This is a close-up image, the affected area is the leg:
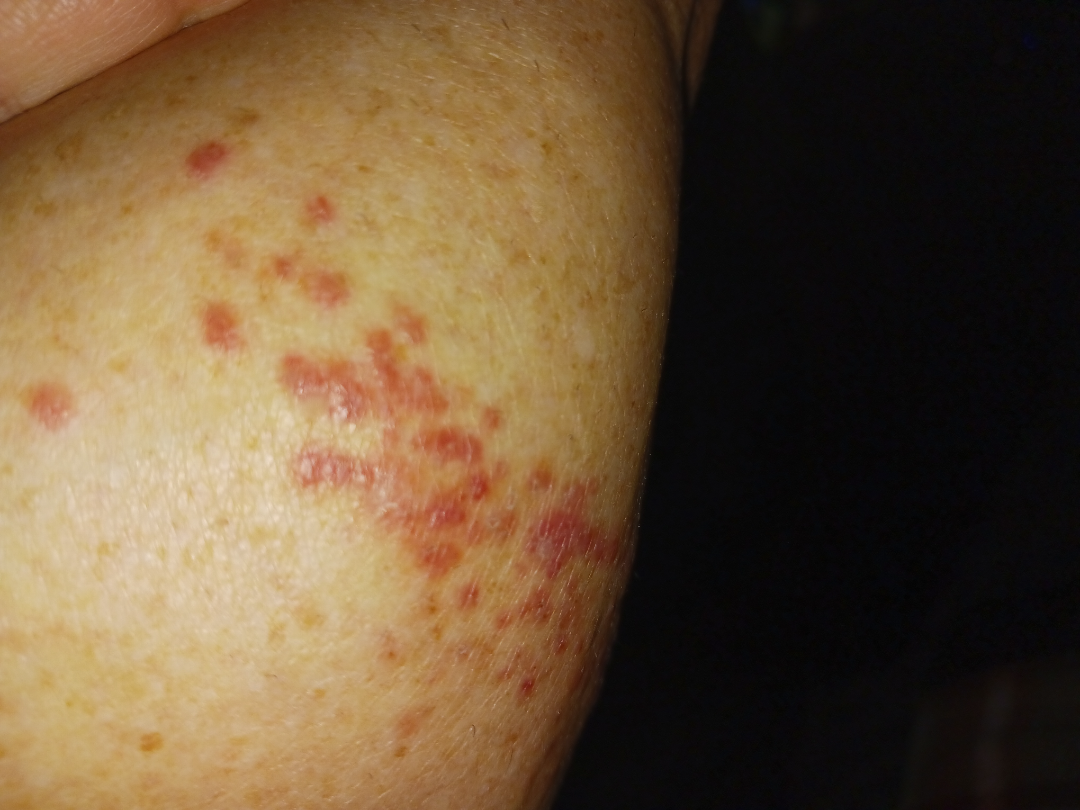Background: No constitutional symptoms were reported. The patient considered this a rash. Texture is reported as raised or bumpy. Present for one to four weeks. Findings: Reviewed remotely by one dermatologist: the differential is split between Pigmented purpuric eruption and Allergic Contact Dermatitis.